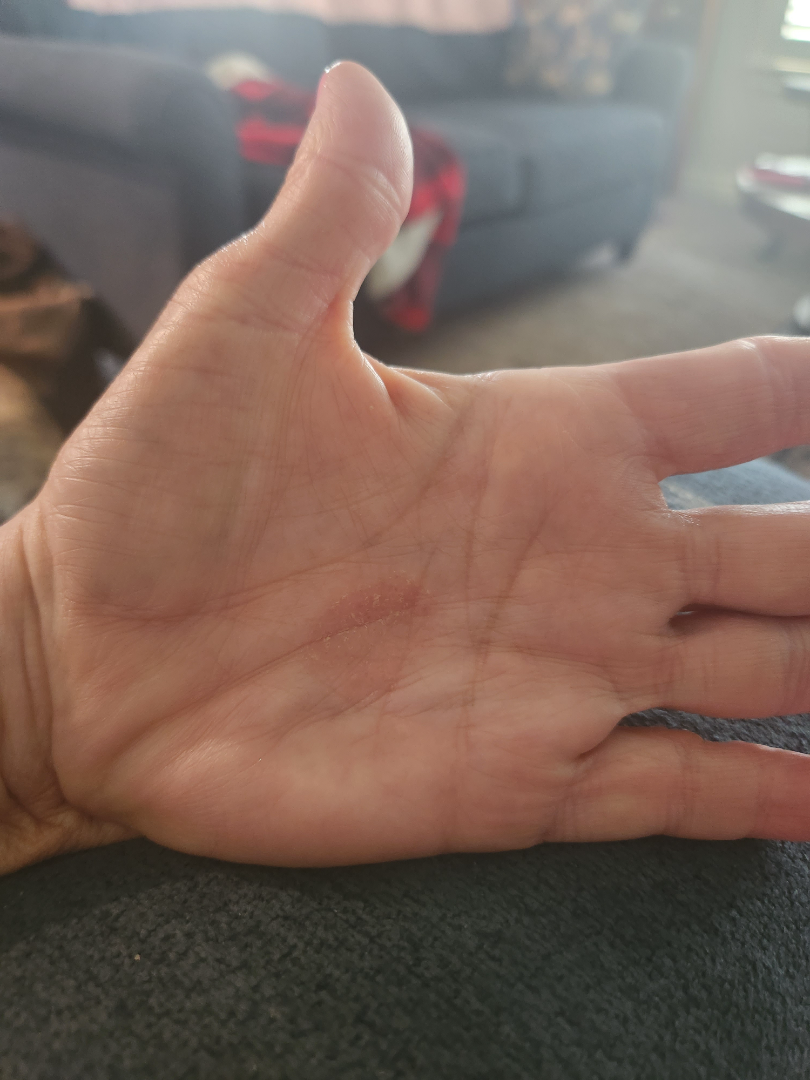patient_category: a rash
shot_type: at a distance
body_site: palm
duration: one to four weeks
symptoms:
  - itching
  - burning
texture:
  - raised or bumpy
  - rough or flaky
differential:
  tied_lead:
    - Psoriasis
    - Eczema